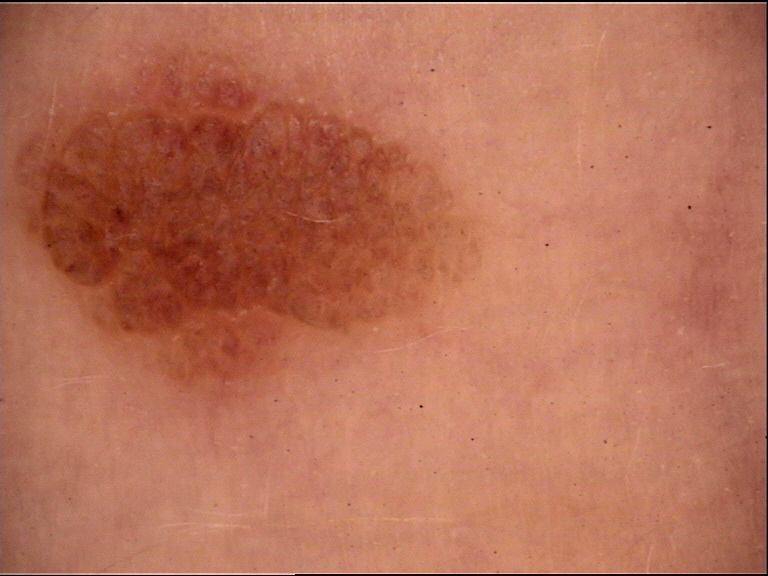Findings: The morphology is that of a banal lesion. Impression: The diagnostic label was a compound nevus.